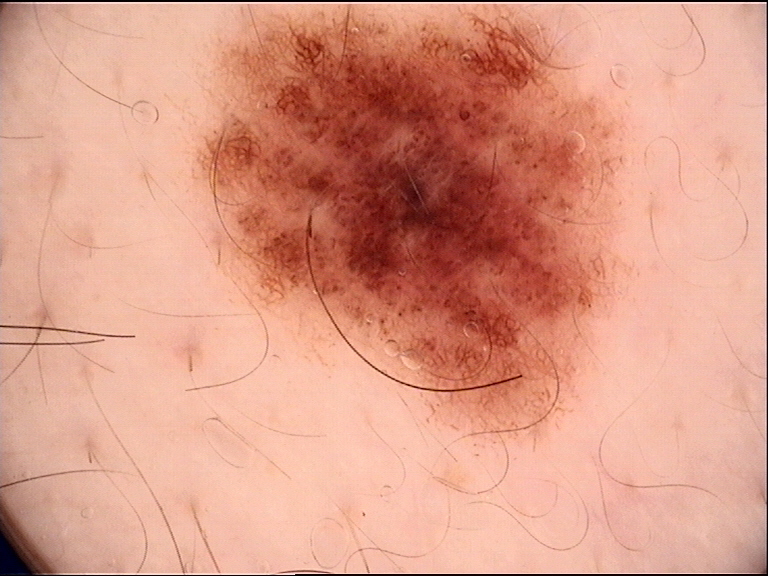{
  "image": "dermoscopy",
  "diagnosis": {
    "name": "dysplastic junctional nevus",
    "code": "jd",
    "malignancy": "benign",
    "super_class": "melanocytic",
    "confirmation": "expert consensus"
  }
}